The patient is 30–39, female. The photo was captured at a distance:
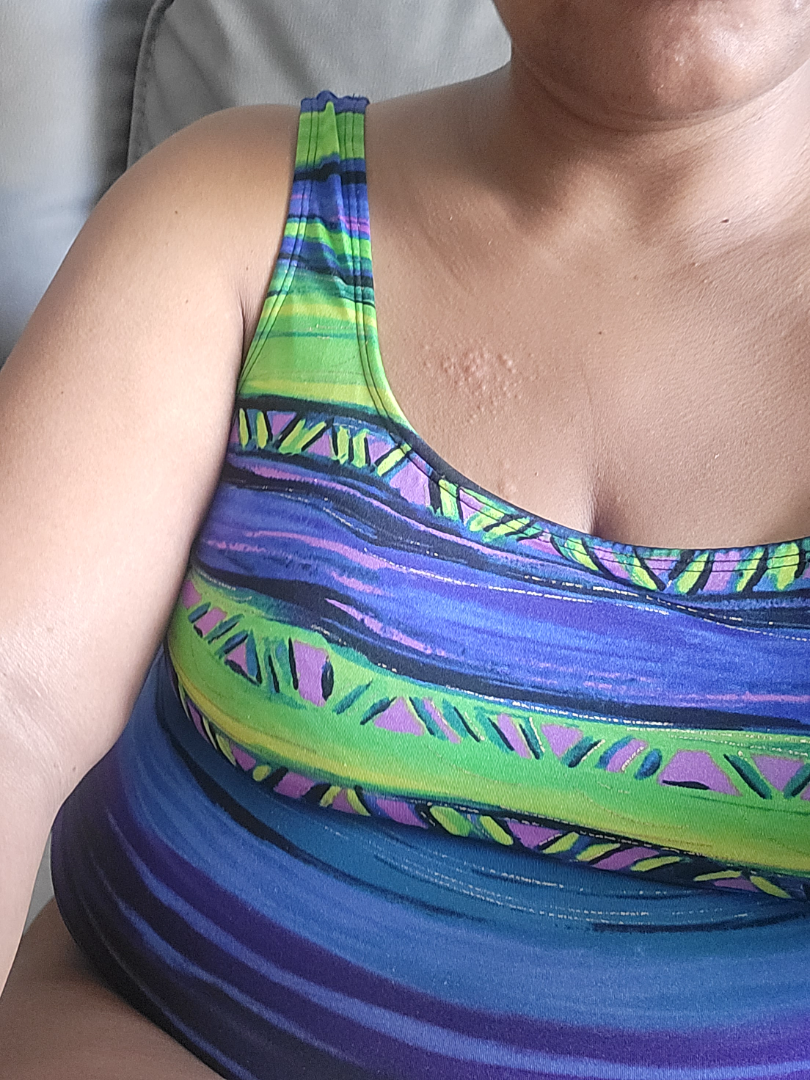dermatologist impression=the differential, in no particular order, includes Insect Bite, Herpes Zoster and Allergic Contact Dermatitis.